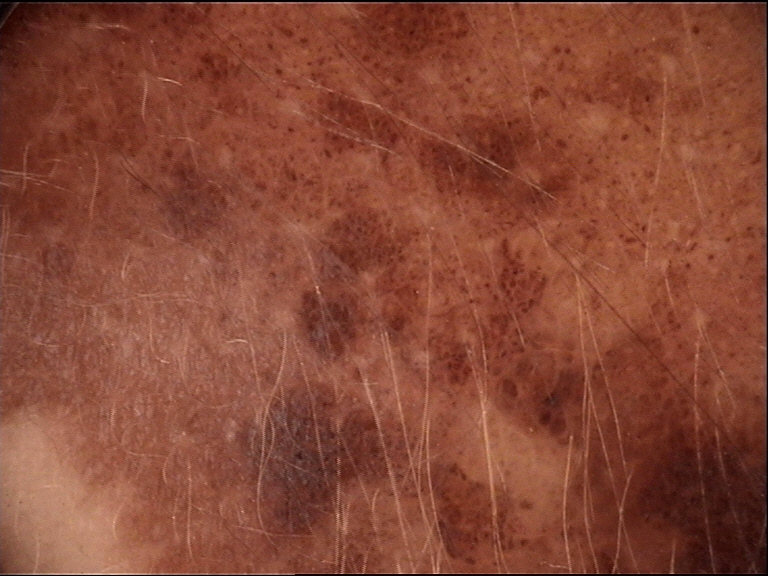Findings: The architecture is that of a banal lesion. Impression: The diagnosis was a congenital junctional nevus.